A dermoscopic image of a skin lesion.
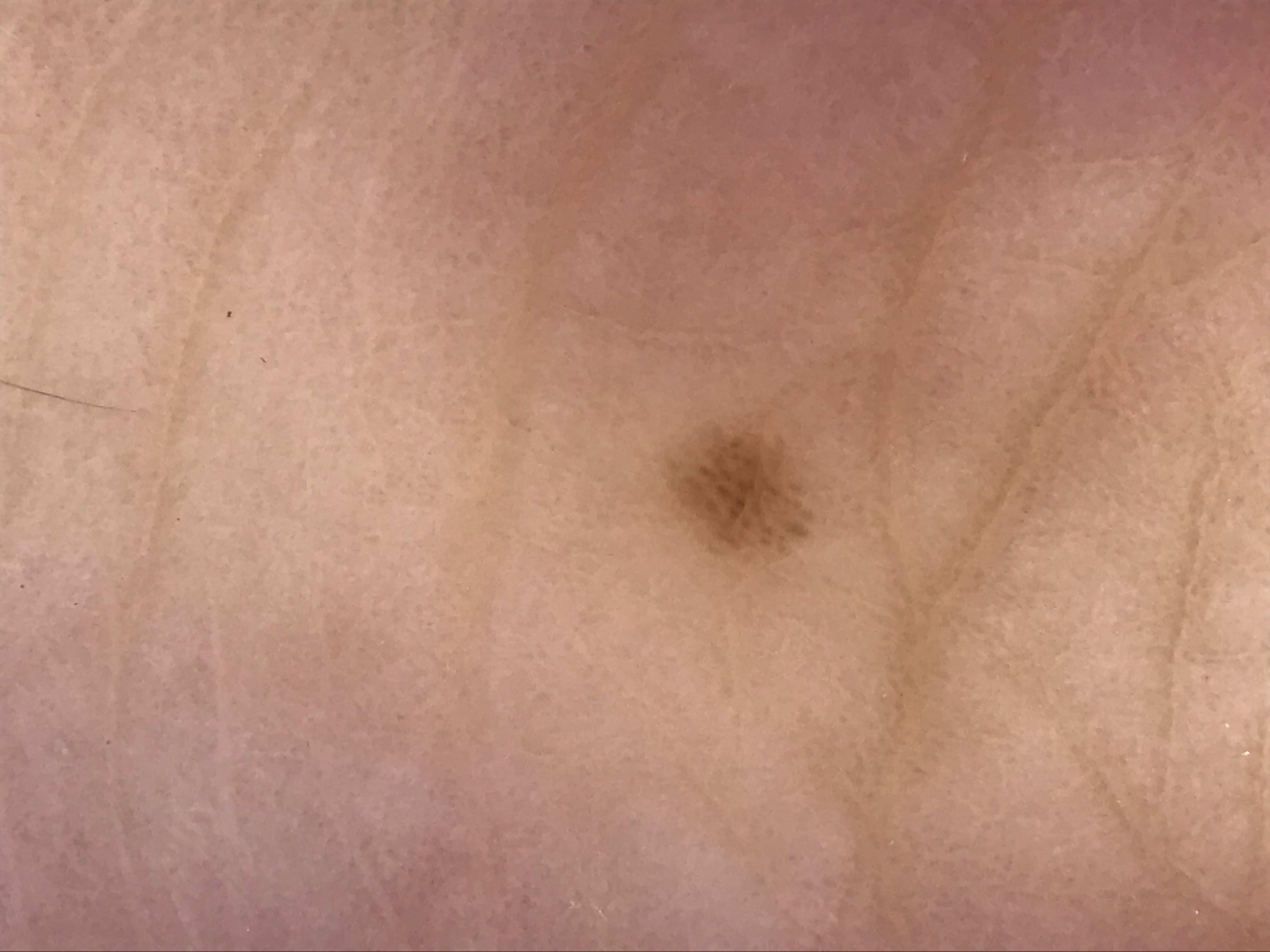The architecture is that of a banal lesion.
The diagnostic label was an acral junctional nevus.